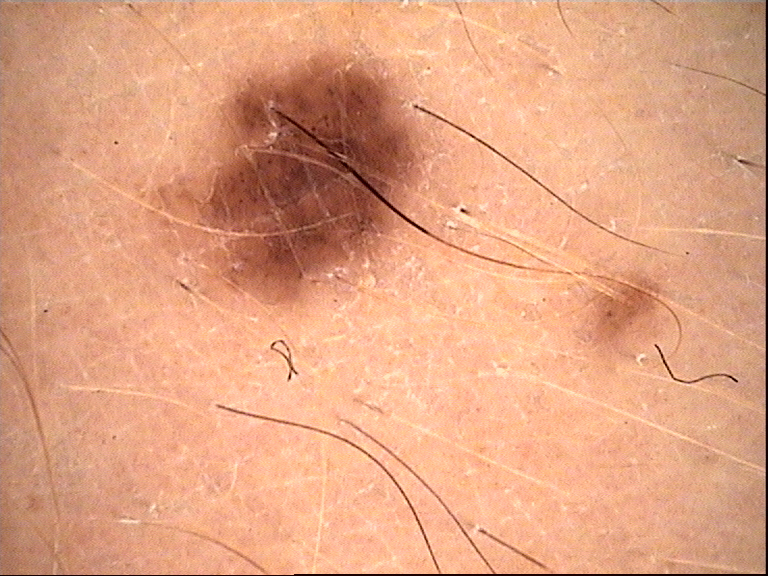The diagnosis was a benign lesion — a dysplastic junctional nevus.